The patient is a male aged 18–29. The affected area is the arm. The photograph is a close-up of the affected area — 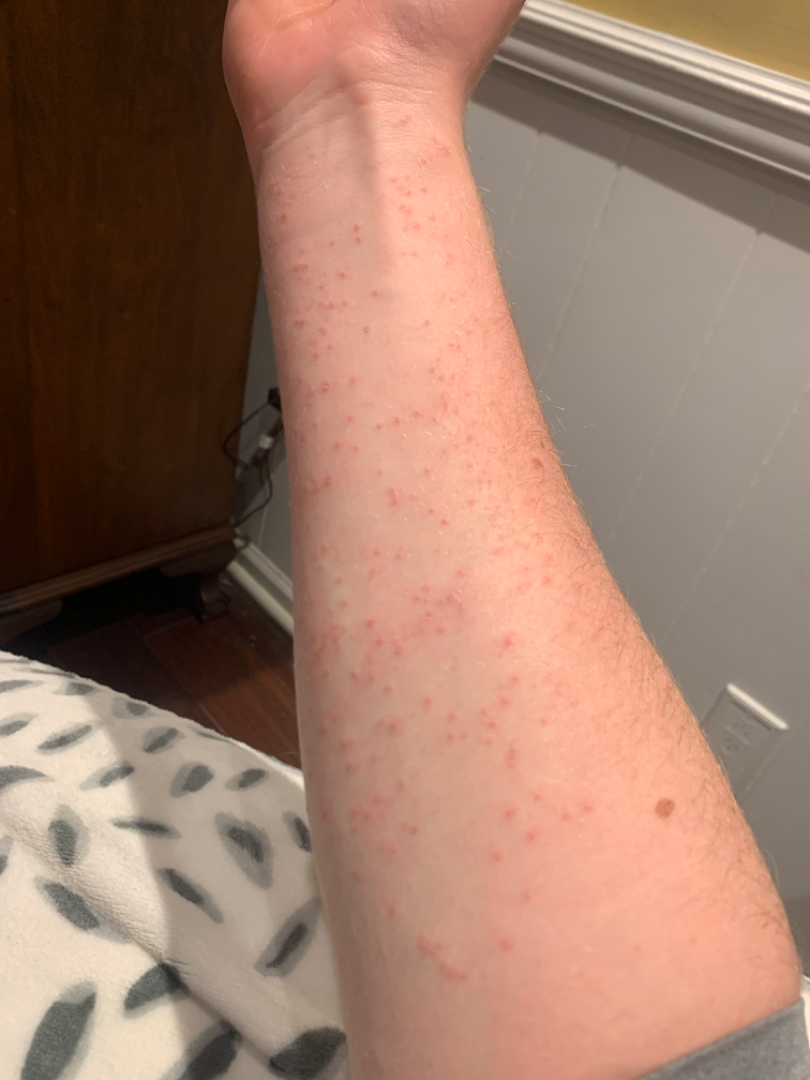Review: Reviewed remotely by one dermatologist: the leading consideration is Eczema; also consider Miliaria; possibly Folliculitis.